A close-up photograph; the lesion involves the arm and front of the torso: 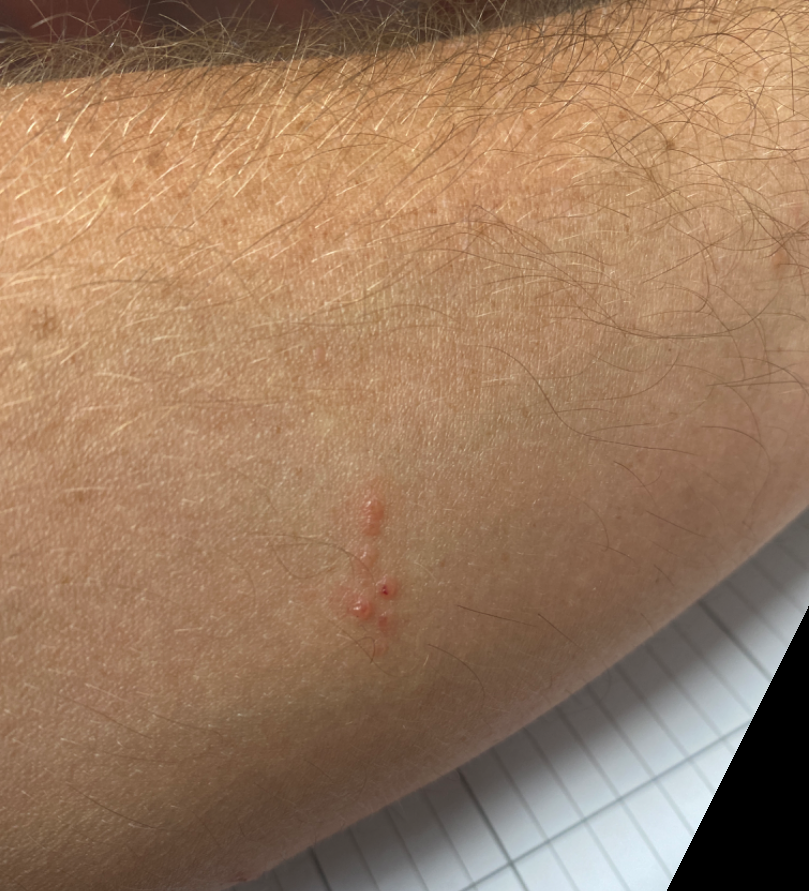assessment: unable to determine.